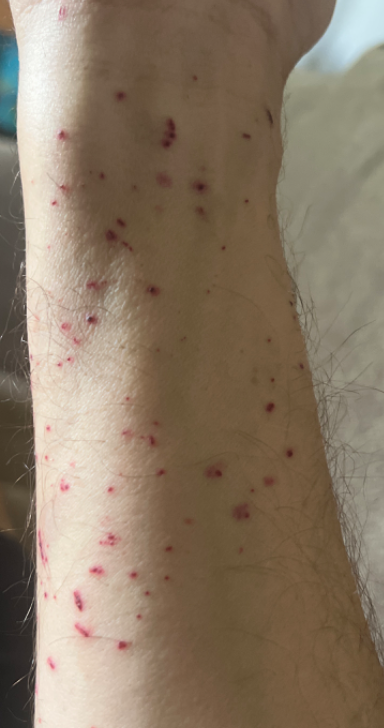Q: Could the case be diagnosed?
A: not assessable
Q: What is the framing?
A: at a distance